A dermatoscopic image of a skin lesion · a male subject approximately 45 years of age · recorded as FST II.
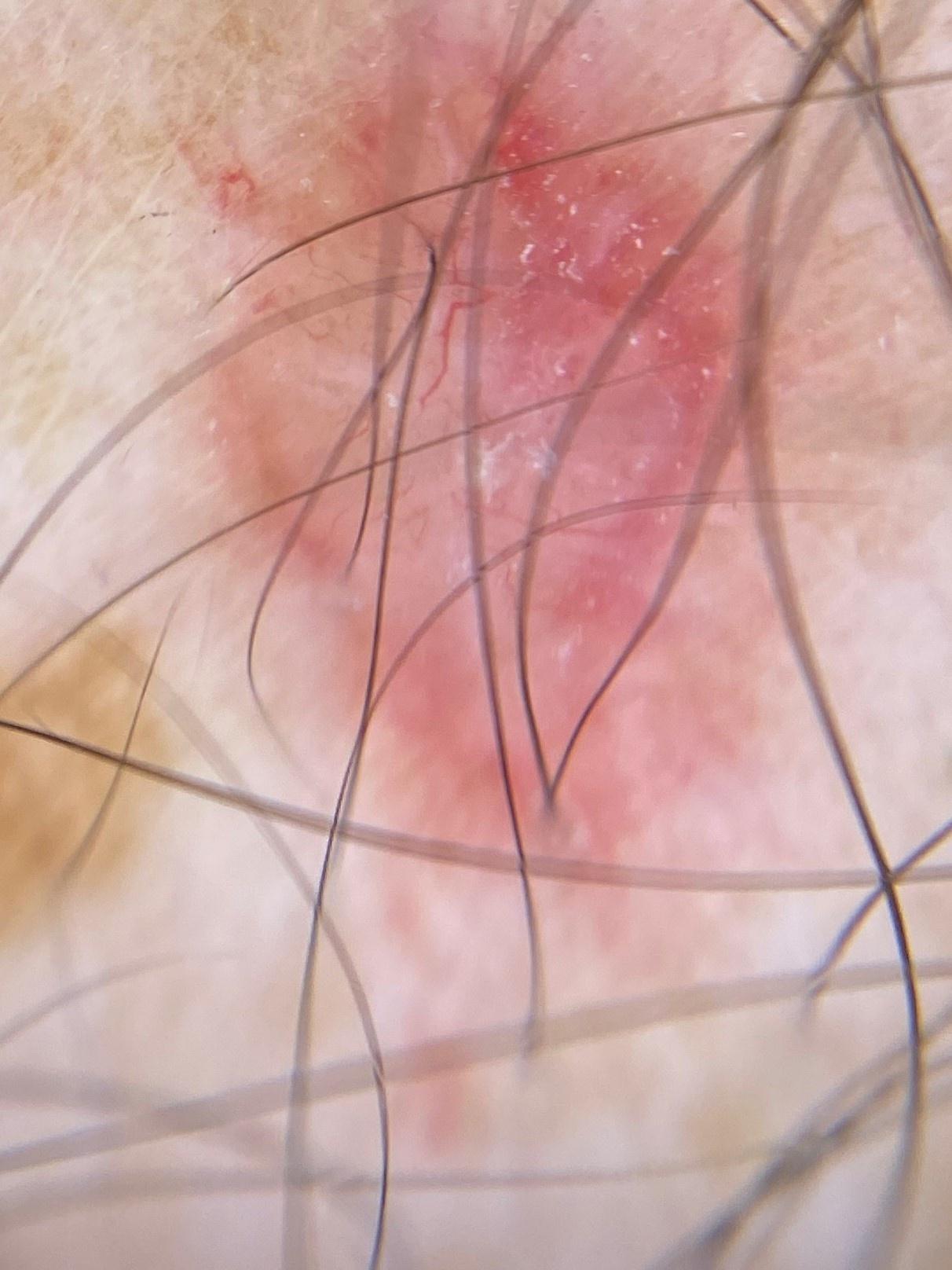Summary: The lesion was found on the trunk (the anterior trunk). Conclusion: Histopathologically confirmed as a malignancy — a basal cell carcinoma.